A dermoscopic image of a skin lesion:
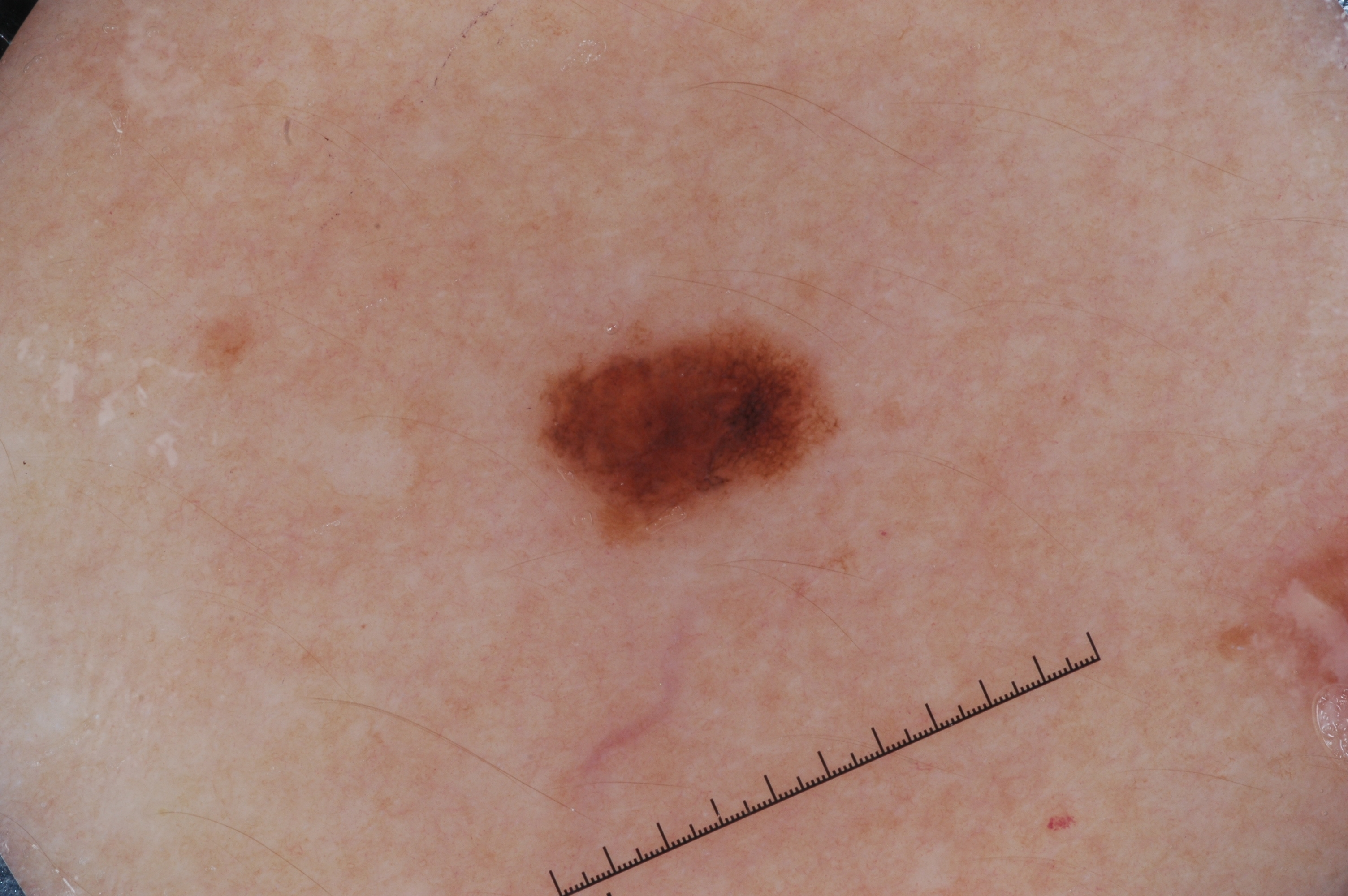Summary: The dermoscopic pattern shows pigment network, with no streaks, milia-like cysts, or negative network. As (left, top, right, bottom), lesion location: 537/322/832/546. Assessment: Diagnosed as a melanocytic nevus.